This is a dermoscopic photograph of a skin lesion — 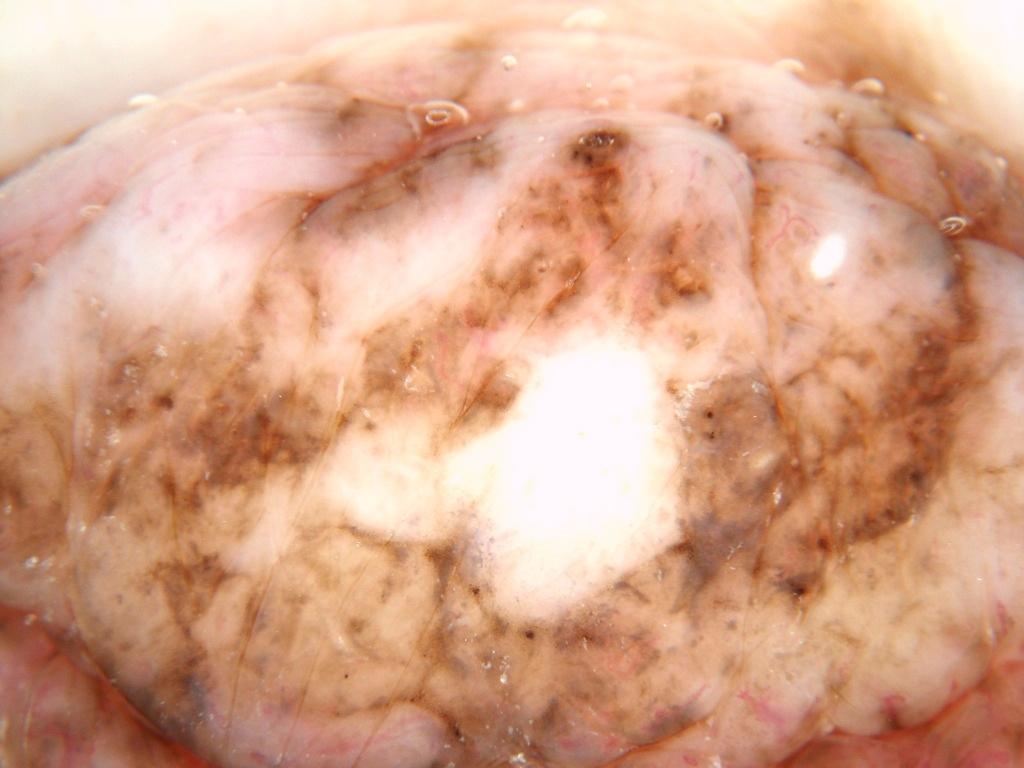Summary: The lesion extends across the full dermoscopic field. Impression: Consistent with a benign skin lesion.